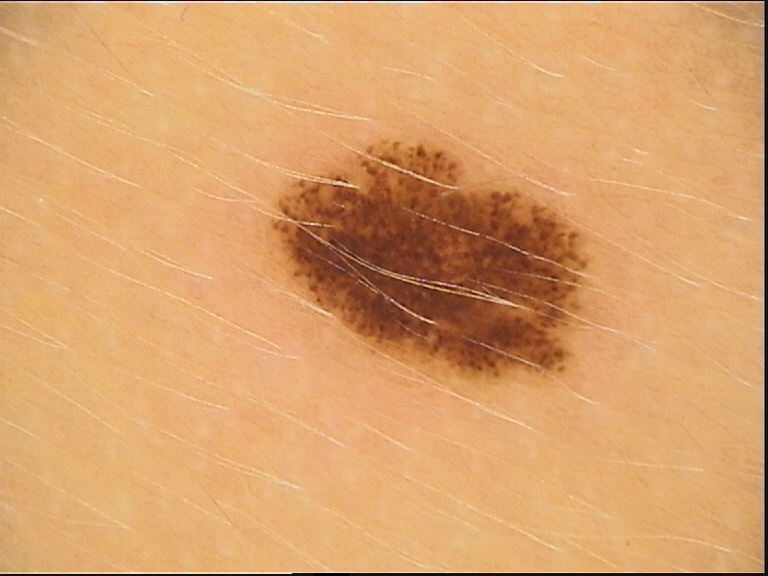The diagnosis was a benign lesion — a dysplastic junctional nevus.